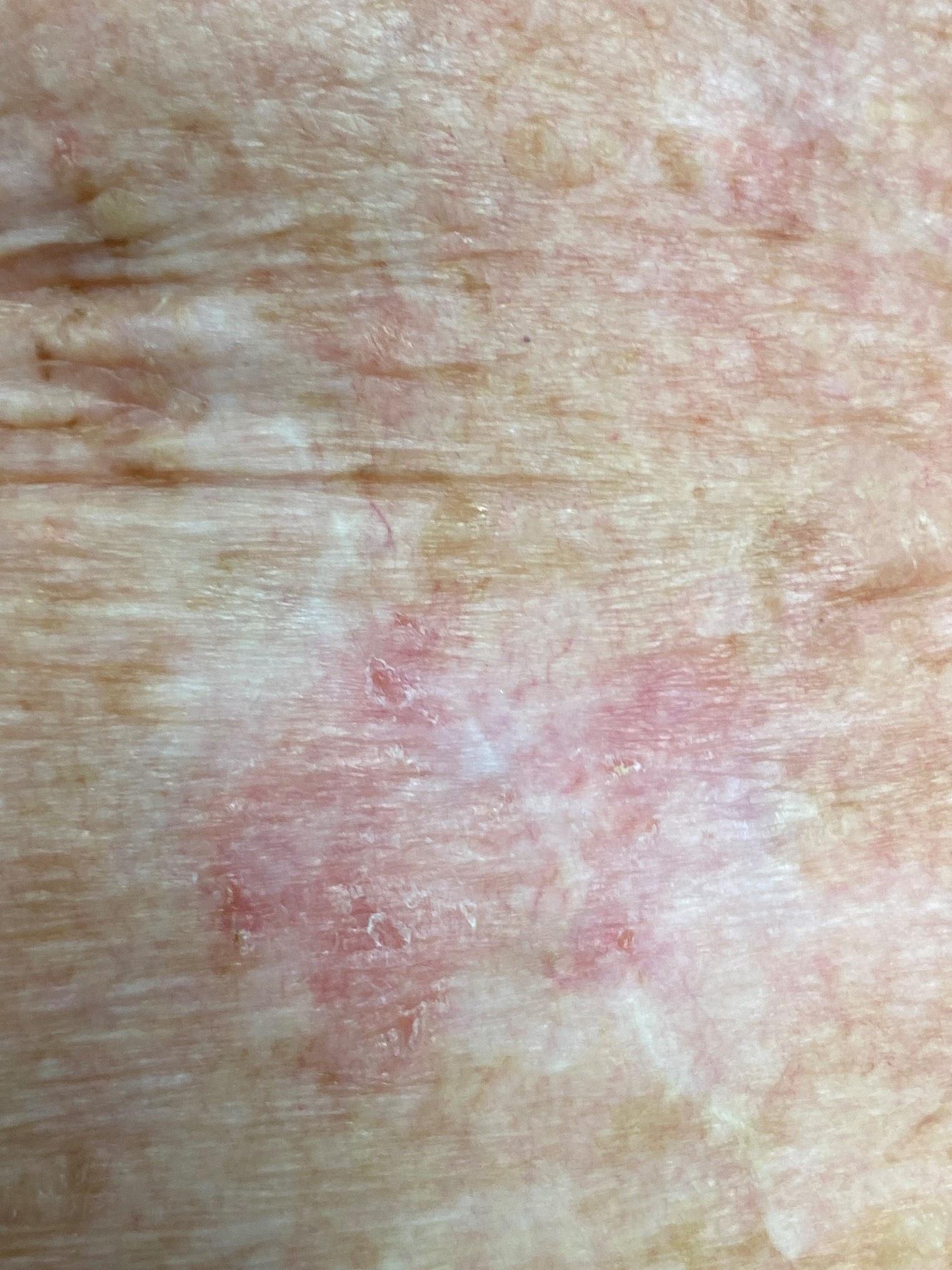Case:
– FST · I
– patient · female, aged approximately 80
– modality · clinical photograph
– body site · the anterior trunk
– pathology · Basal cell carcinoma (biopsy-proven)